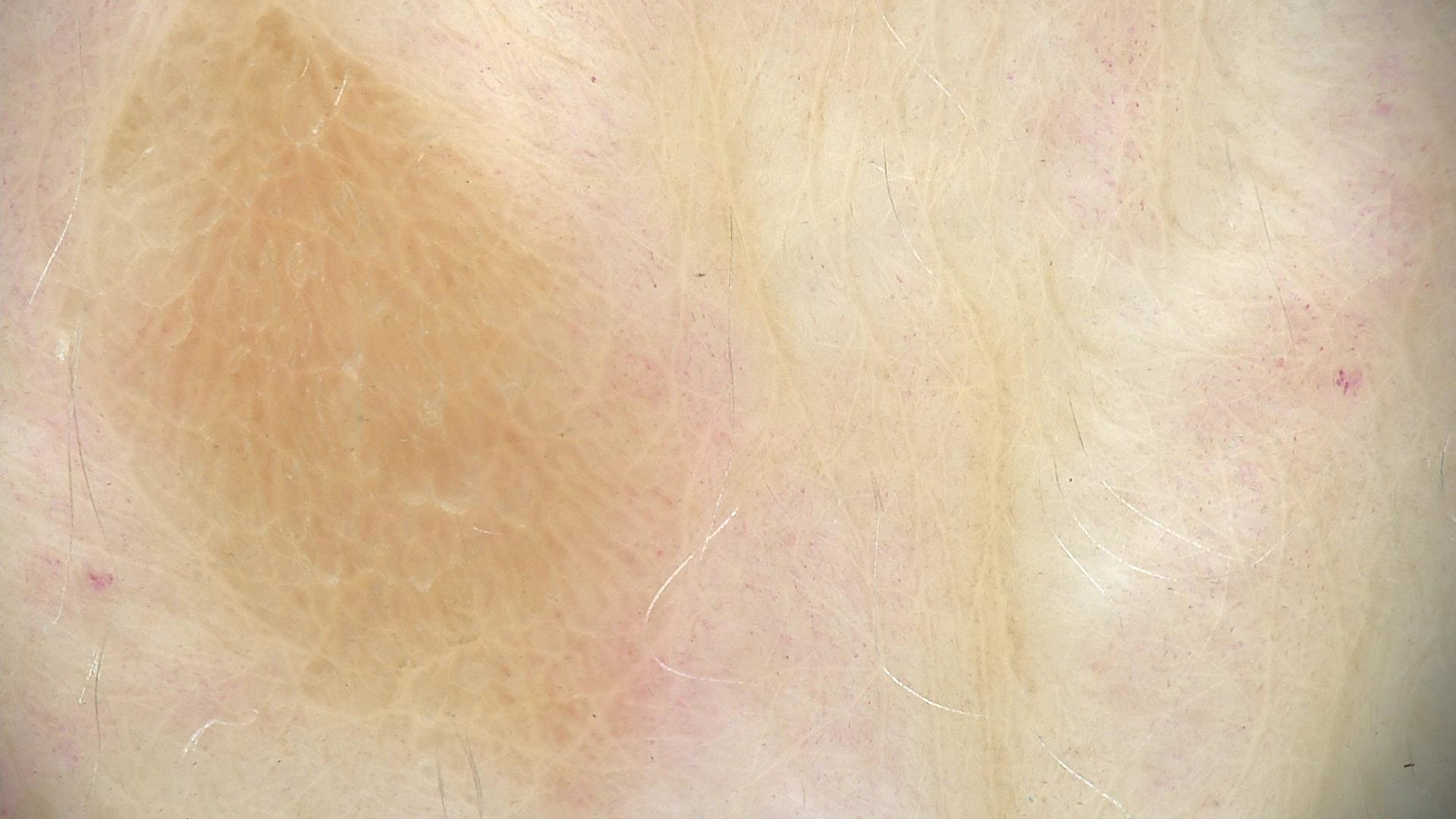diagnosis = seborrheic keratosis (expert consensus).